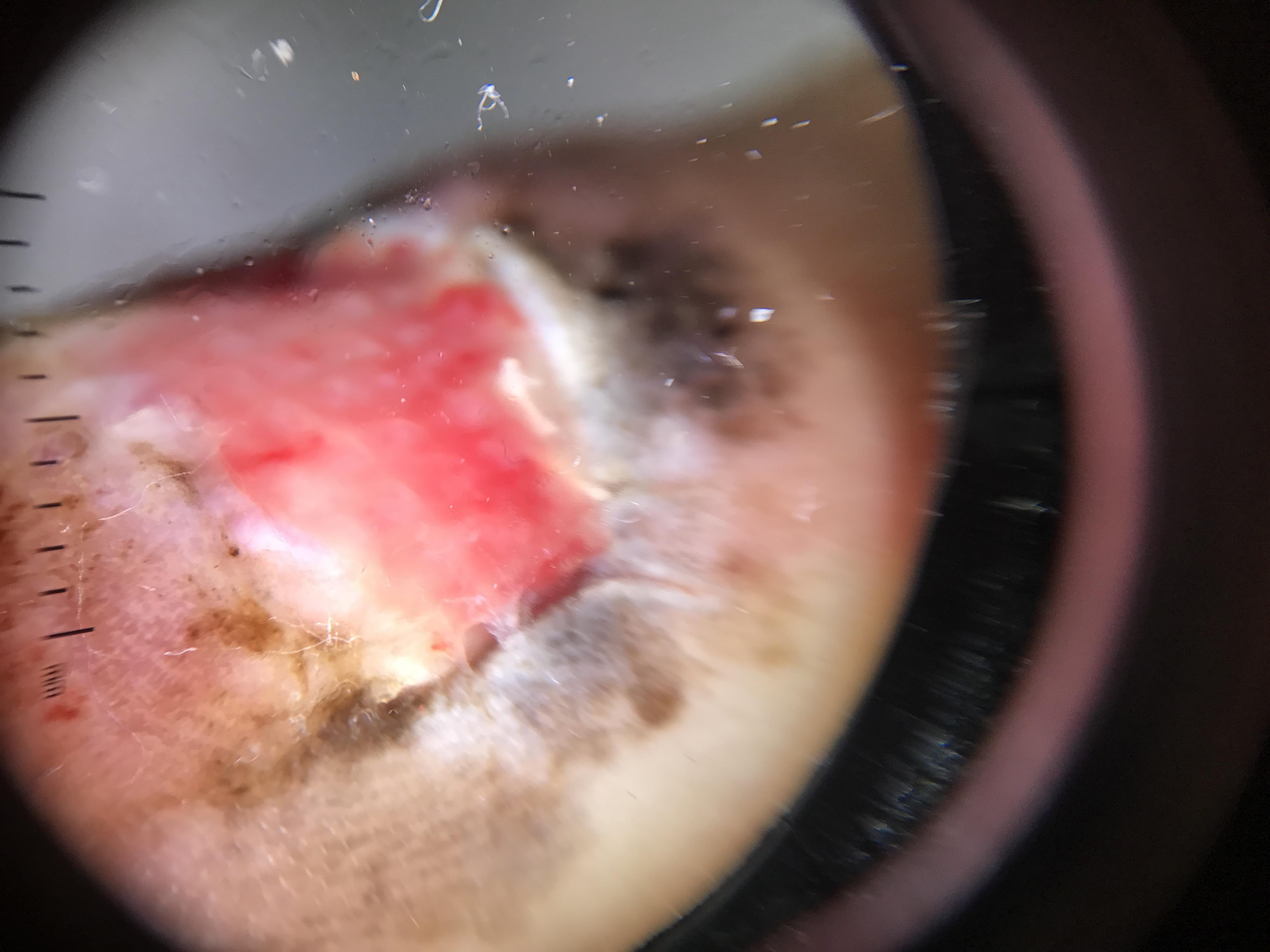| feature | finding |
|---|---|
| diagnostic label | Melanoma (biopsy-proven) |